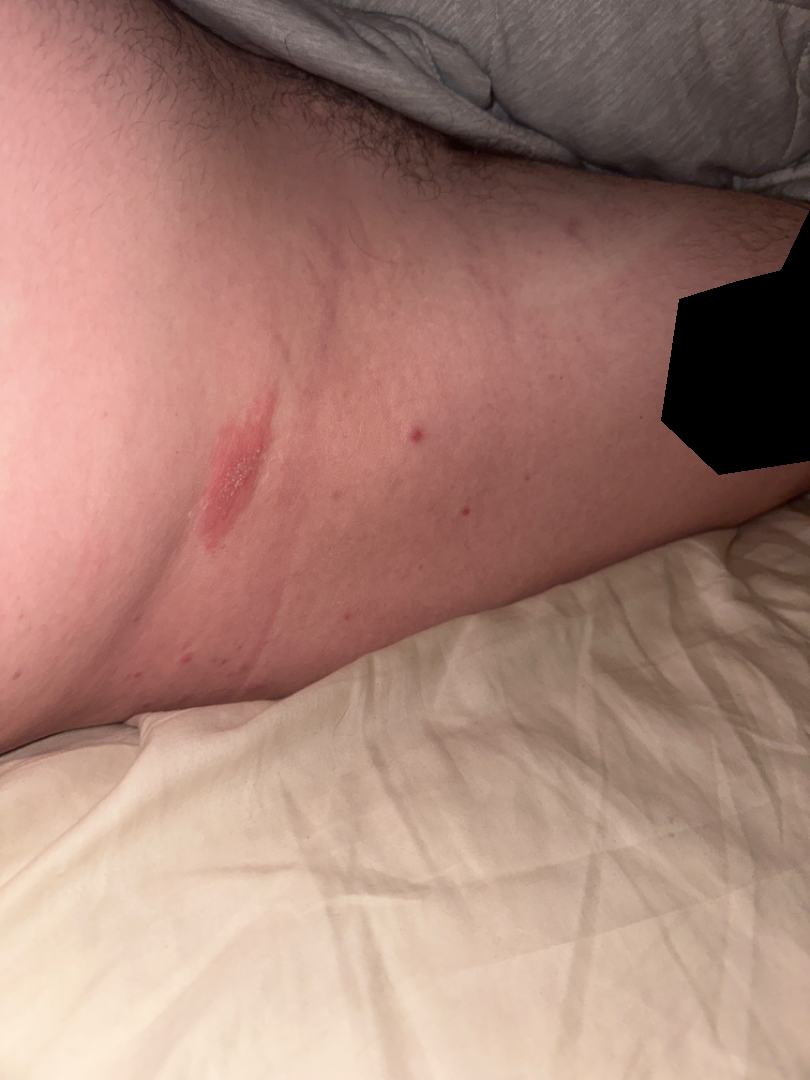The patient described the issue as a rash. Reported duration is about one day. This image was taken at a distance. The patient reported no systemic symptoms. Symptoms reported: burning and itching. The patient is 30–39, male. Texture is reported as raised or bumpy. Most likely Herpes Simplex; also consider Herpes Zoster.